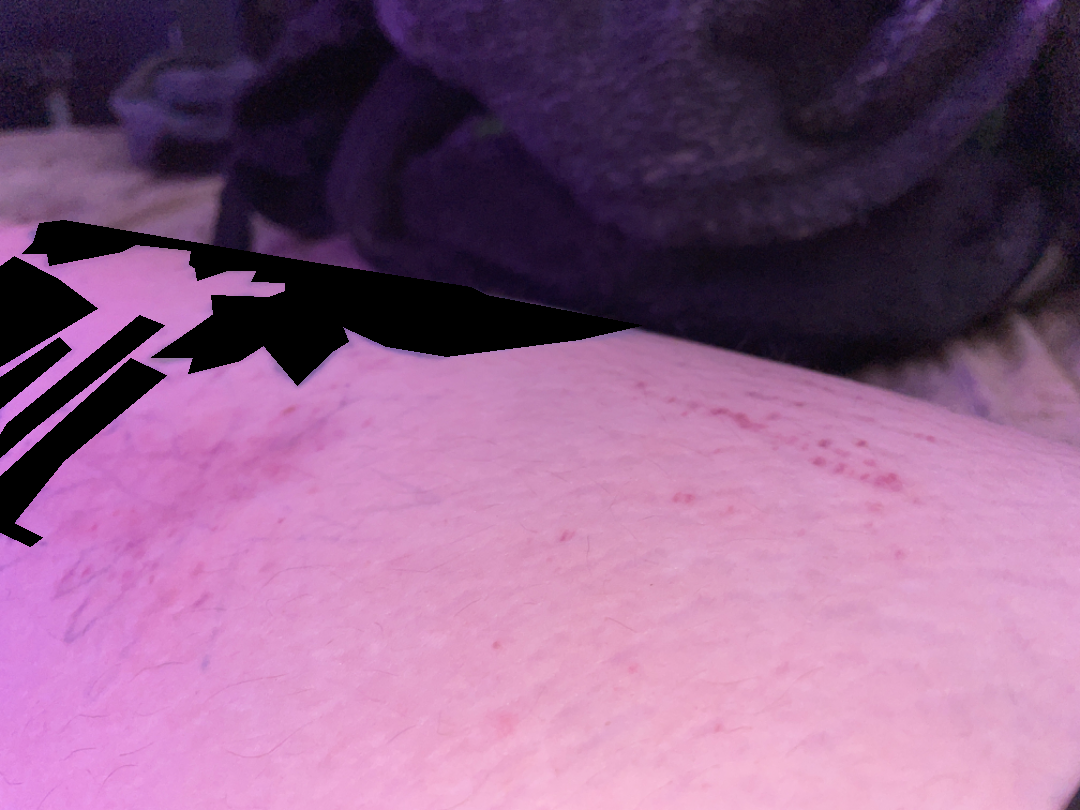assessment: ungradable on photographic review.